The patient reports a family history of skin cancer, a personal history of cancer, and no prior organ transplant. A female patient aged 92. The patient says their skin tans without first burning. Collected as part of a research study, without a referral diagnosis. A dermoscopy image of a skin lesion — 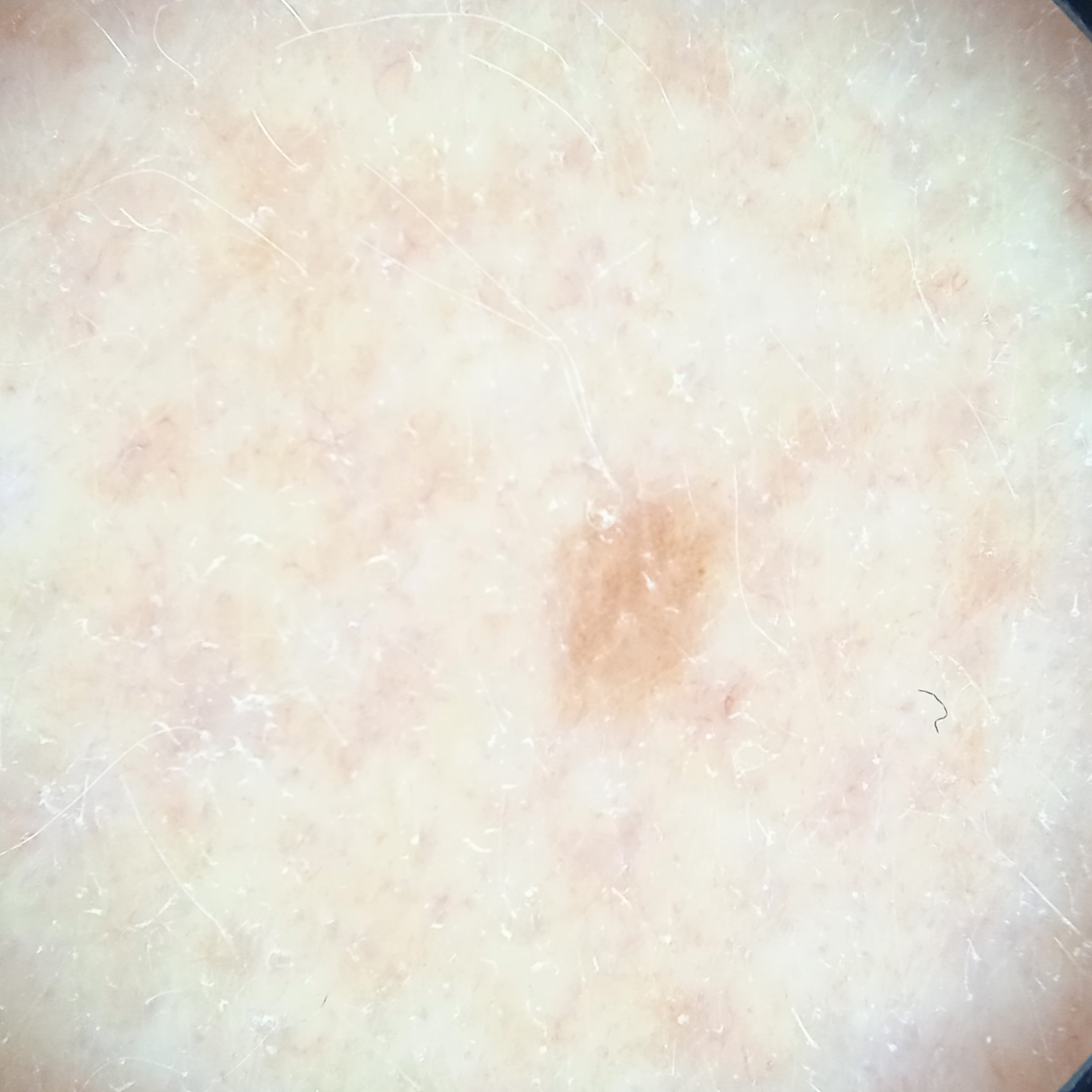| field | value |
|---|---|
| location | the face |
| lesion size | 2.9 mm |
| diagnosis | melanocytic nevus (dermatologist consensus) |